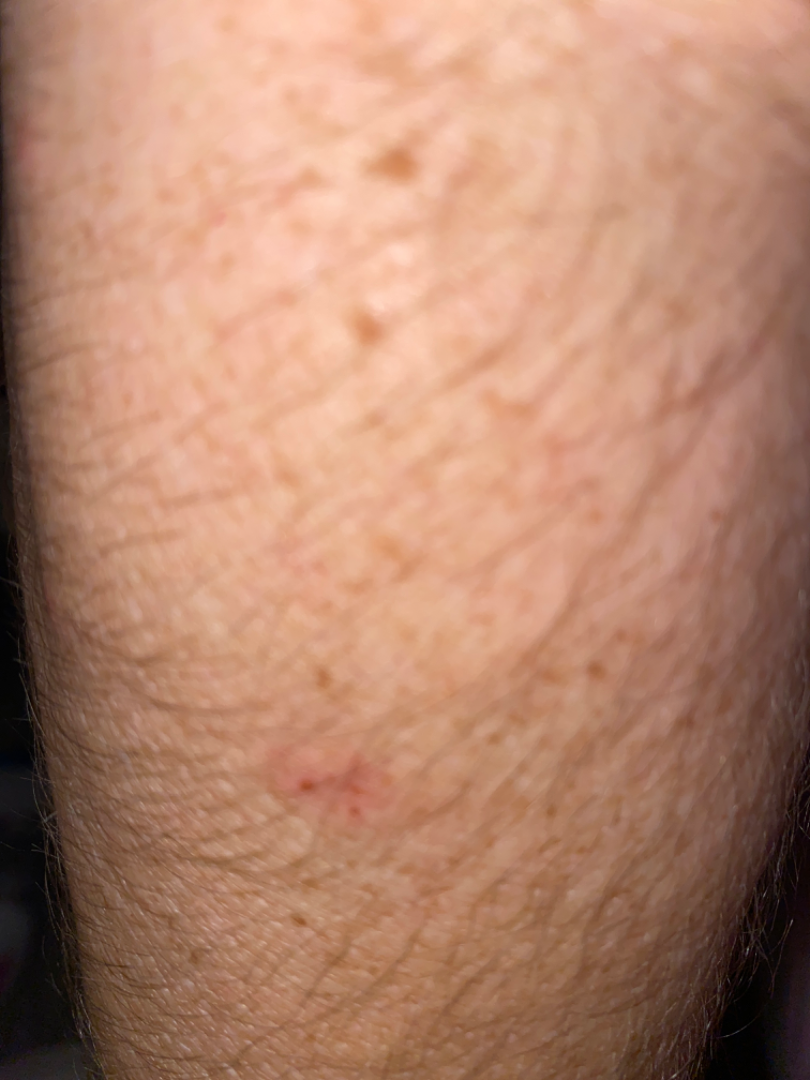On remote review of the image, Insect Bite and Inflicted skin lesions were considered with similar weight.